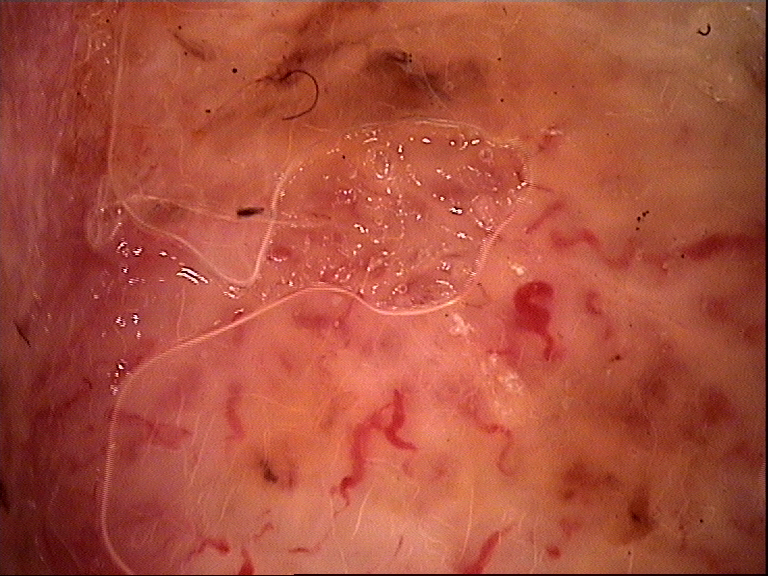Findings:
- class · basal cell carcinoma (biopsy-proven)